A female patient aged 59; a dermoscopy image of a skin lesion; the patient describes having a moderate number of moles:
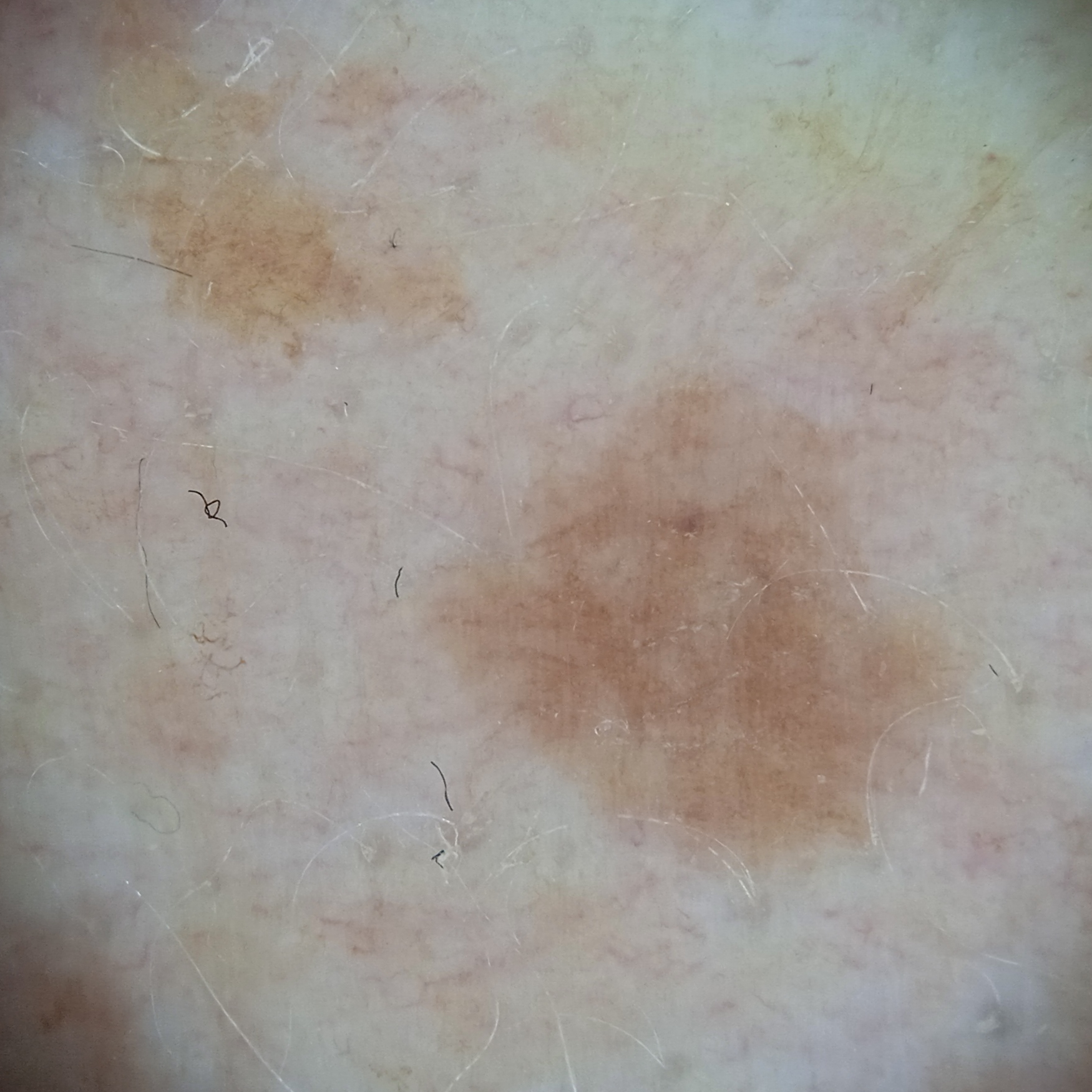Findings:
Located on an arm. Measuring roughly 6.5 mm.
Conclusion:
The dermatologists' assessment was a melanocytic nevus.